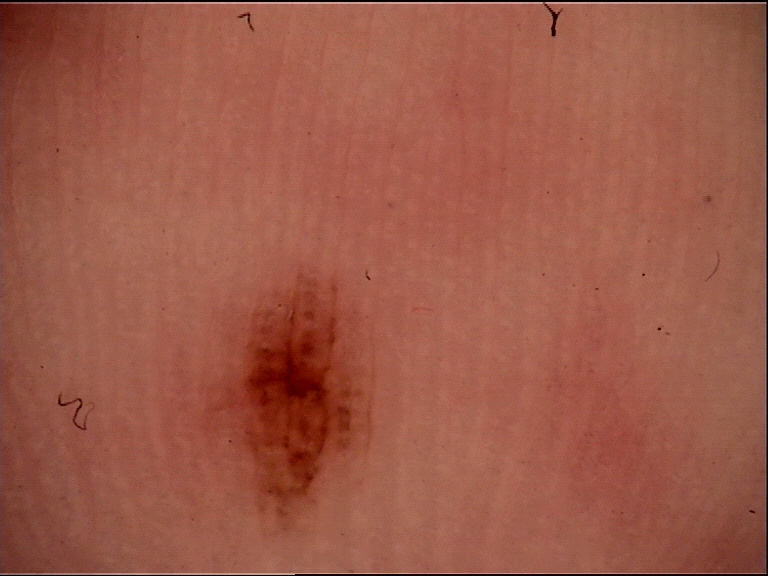A dermoscopy image of a single skin lesion.
Labeled as a banal lesion — an acral junctional nevus.